A dermoscopic image of a skin lesion.
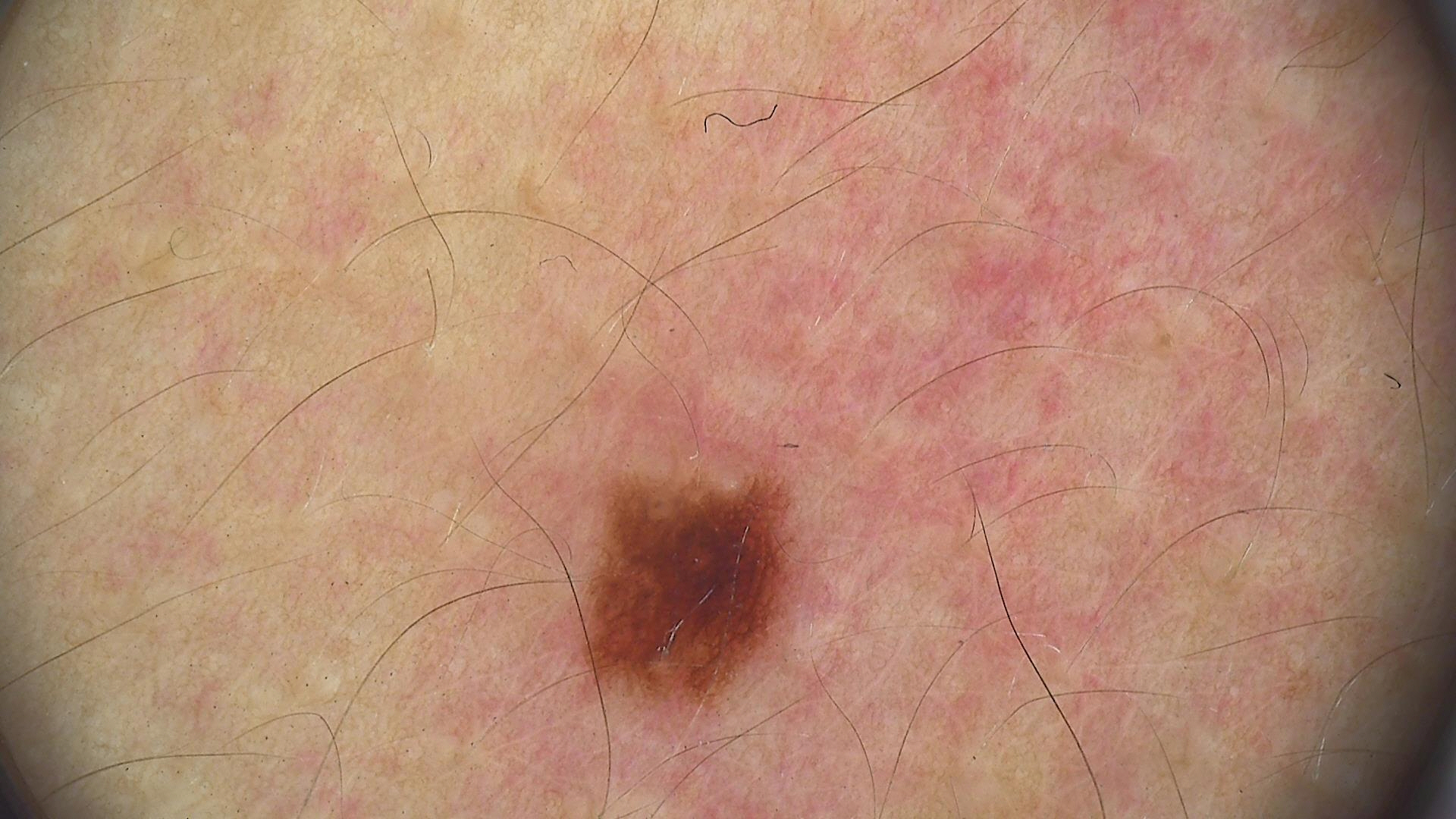The diagnostic label was a dysplastic junctional nevus.